Close-up view.
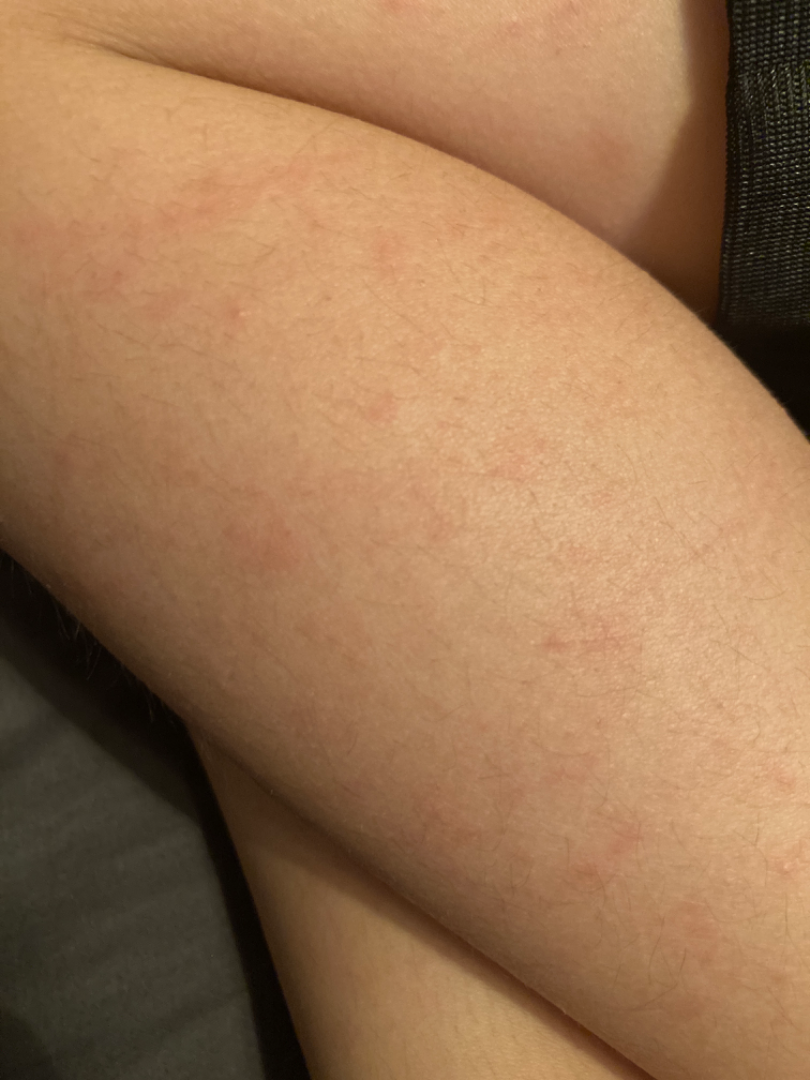assessment: unable to determine.